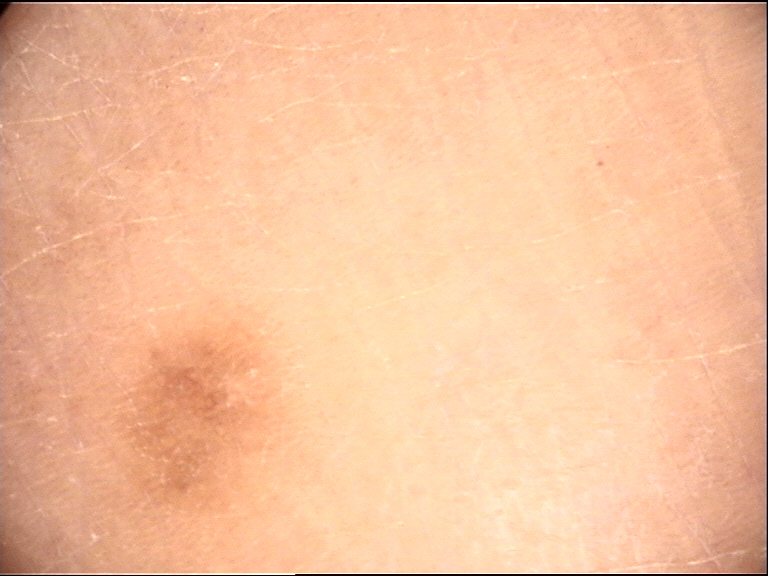| feature | finding |
|---|---|
| label | dermatofibroma (expert consensus) |